A male patient aged approximately 85 or older · contact-polarized dermoscopy of a skin lesion · recorded as Fitzpatrick skin type II — 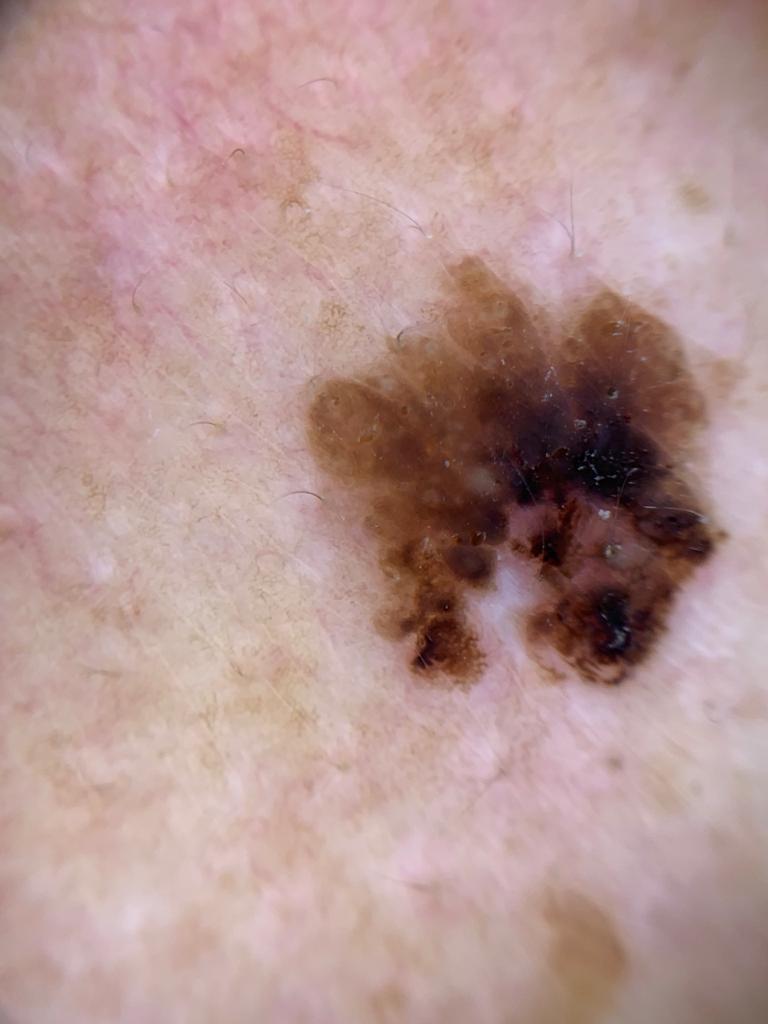Q: Where is the lesion located?
A: an upper extremity
Q: What did the workup show?
A: Seborrheic keratosis (biopsy-proven)